A dermoscopic close-up of a skin lesion: 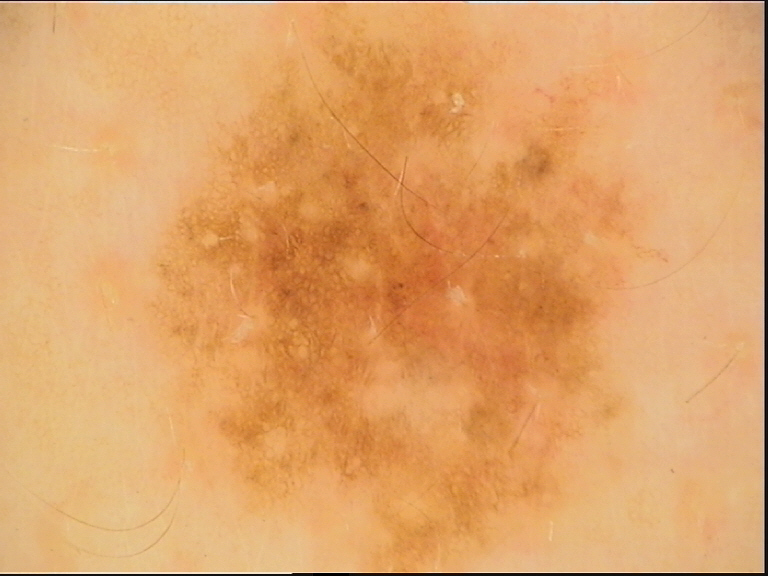Labeled as a benign lesion — a dysplastic junctional nevus.